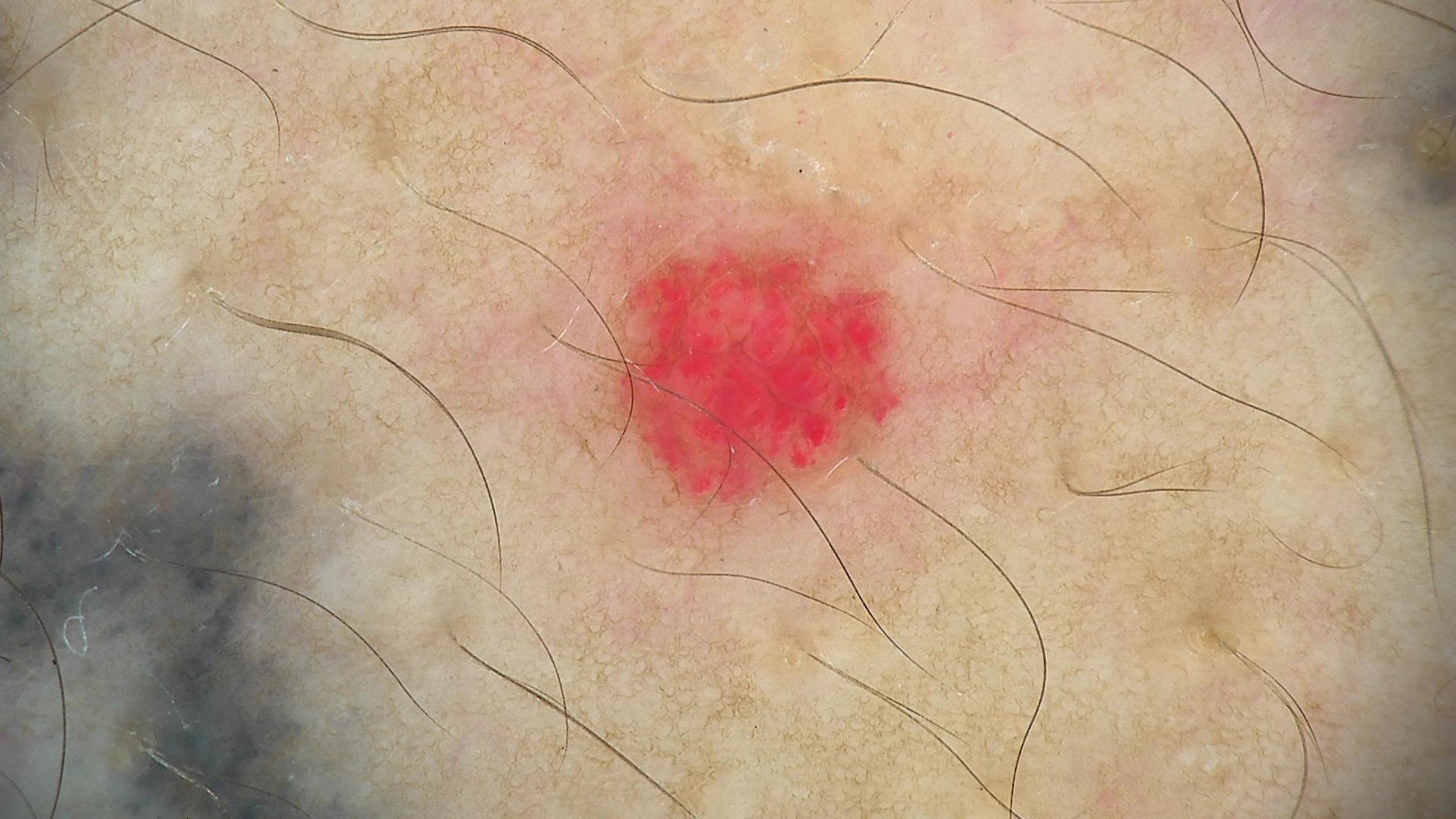image: dermatoscopy
classification: vascular
diagnostic label: hemangioma (expert consensus)